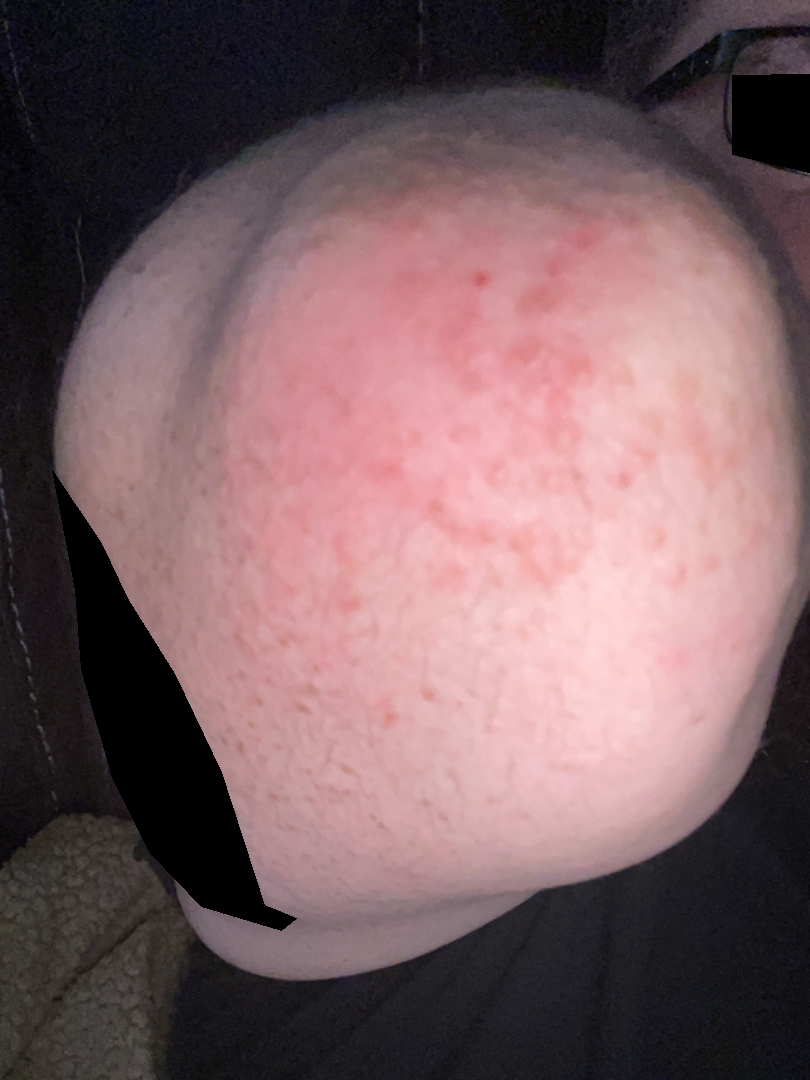The reviewer was unable to grade this case for skin condition. The patient considered this a rash. Symptoms reported: bothersome appearance and itching. The photograph is a close-up of the affected area. The contributor notes the lesion is raised or bumpy. The contributor notes the condition has been present for less than one week. The affected area is the arm, head or neck and front of the torso.